Located on the leg; a close-up photograph:
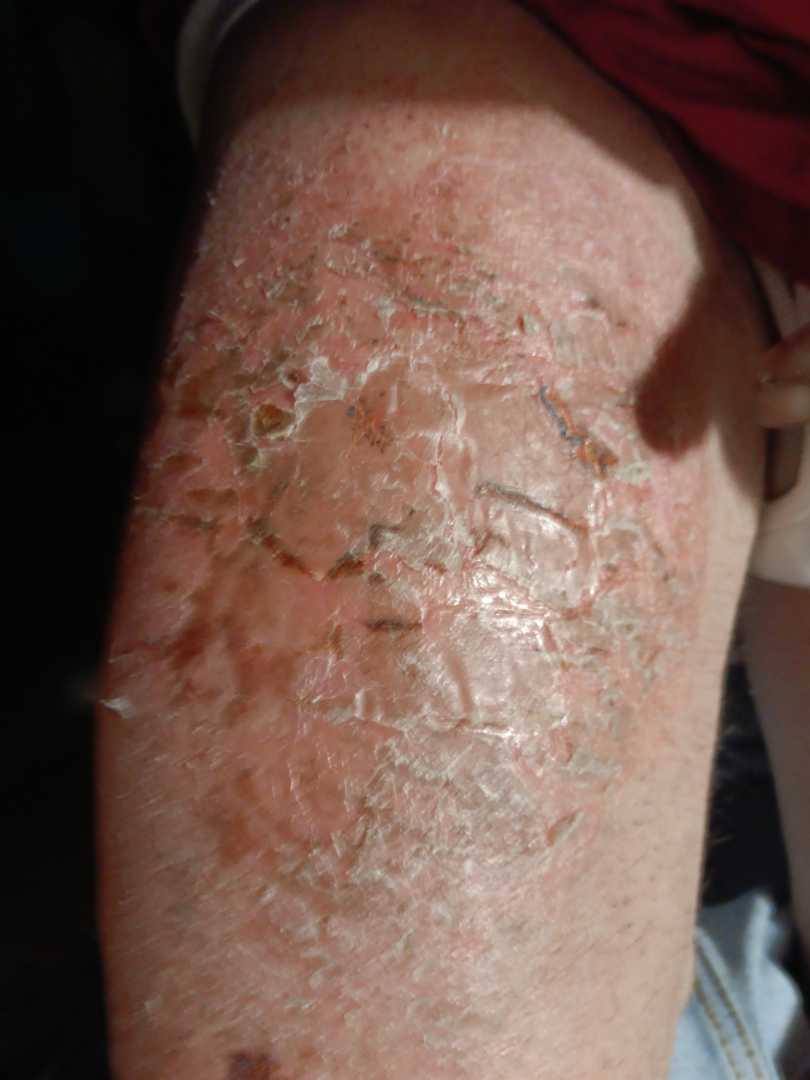Q: Could the case be diagnosed?
A: unable to determine